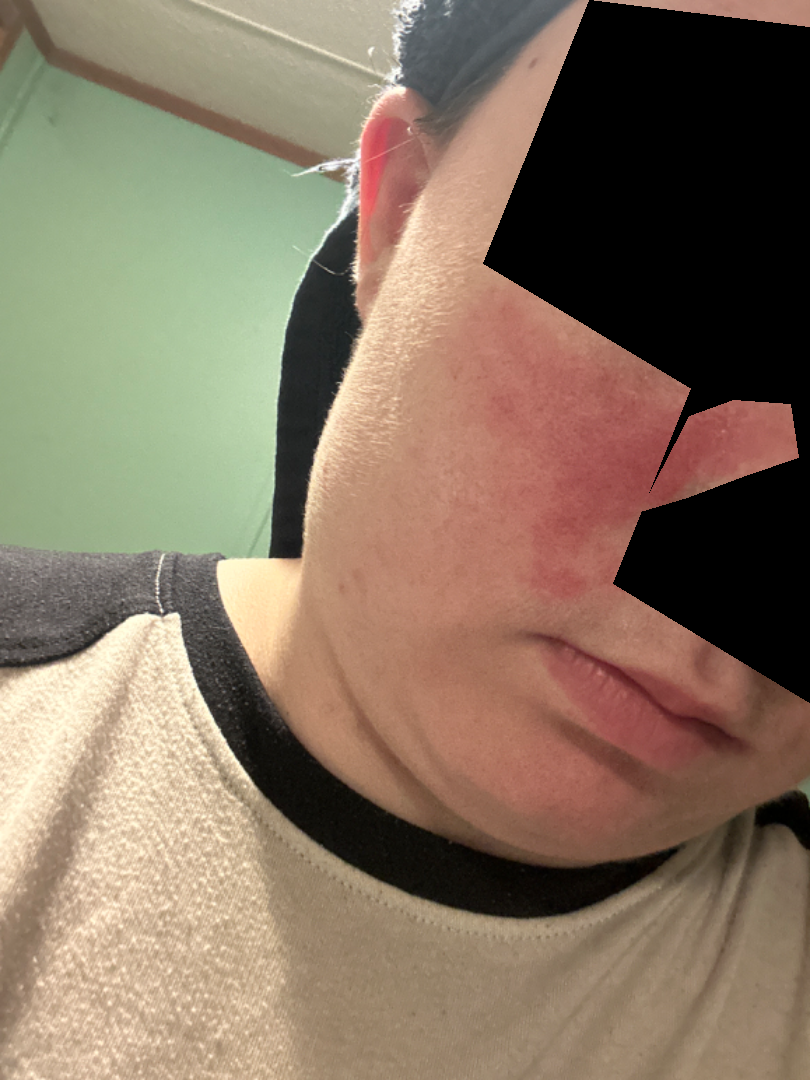Patient information:
The patient considered this a rash. The subject is a female aged 18–29. The lesion involves the head or neck. No associated systemic symptoms reported. The condition has been present for one to three months. Symptoms reported: bothersome appearance. Skin tone: Fitzpatrick phototype II; lay graders estimated Monk Skin Tone 2. The photo was captured at an angle.
Review:
Most likely Rosacea; with consideration of Cutaneous lupus; less probable is Seborrheic Dermatitis; lower on the differential is Erysipelas.